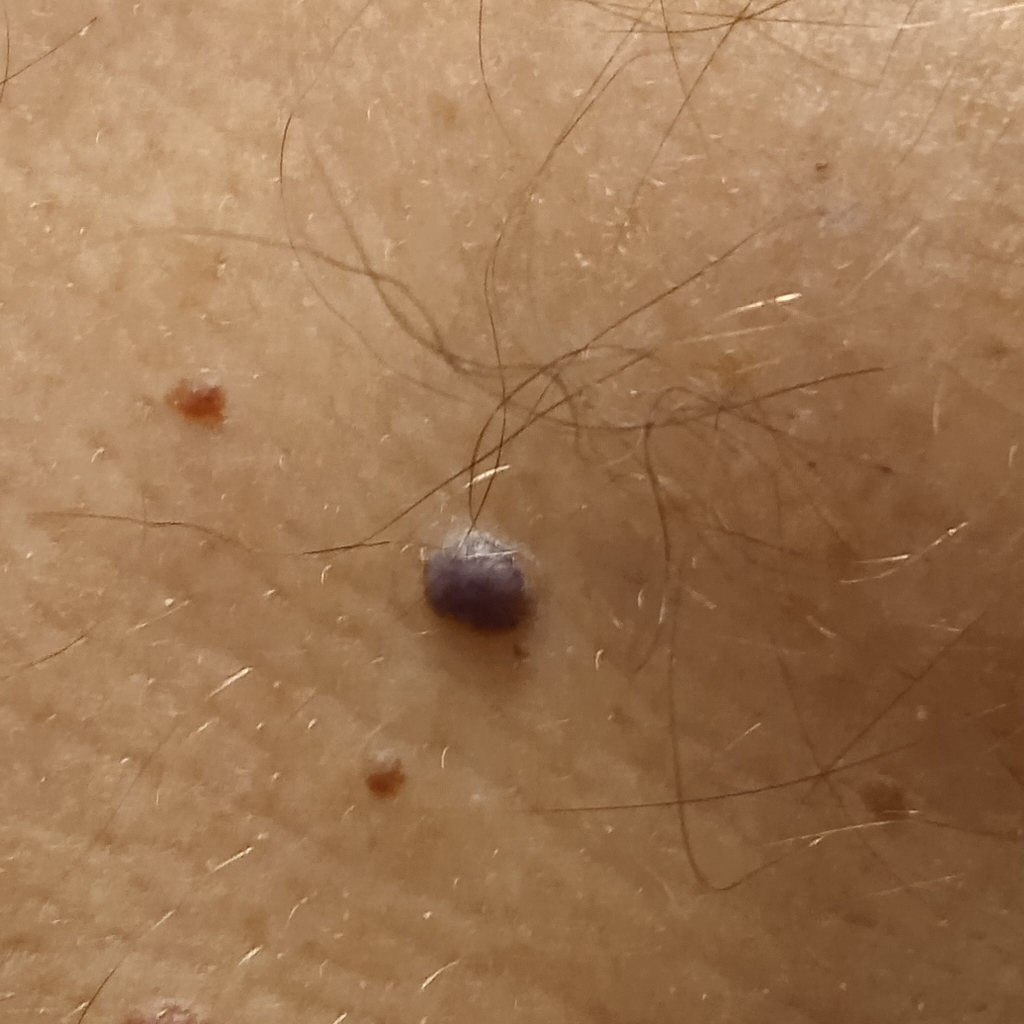clinical context = research study (no referral diagnosis); image = clinical photo; risk factors = a personal history of cancer; sun reaction = skin reddens with sun exposure; body site = the torso; size = 4.7 mm; diagnosis = angioma (dermatologist consensus).